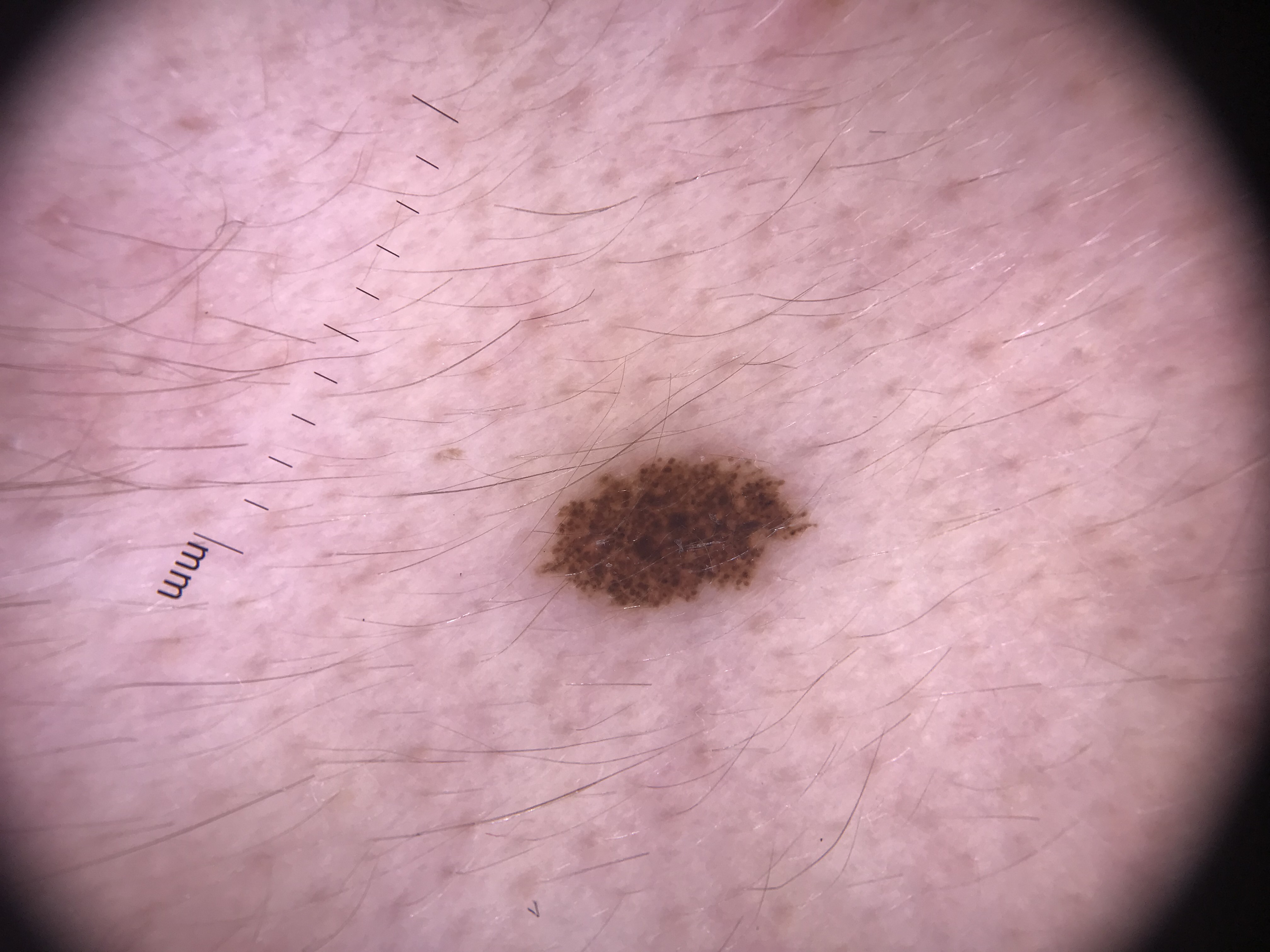assessment=dysplastic junctional nevus (expert consensus)